A dermoscopic photograph of a skin lesion.
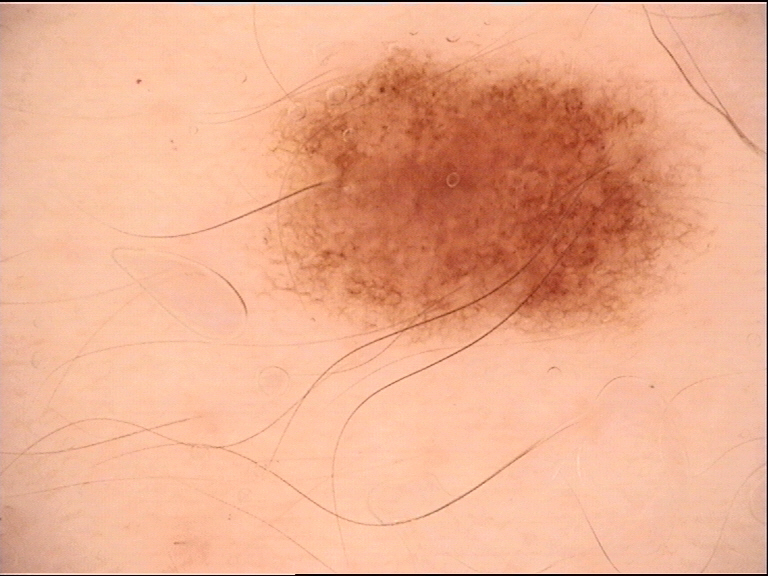Impression:
Classified as a dysplastic junctional nevus.